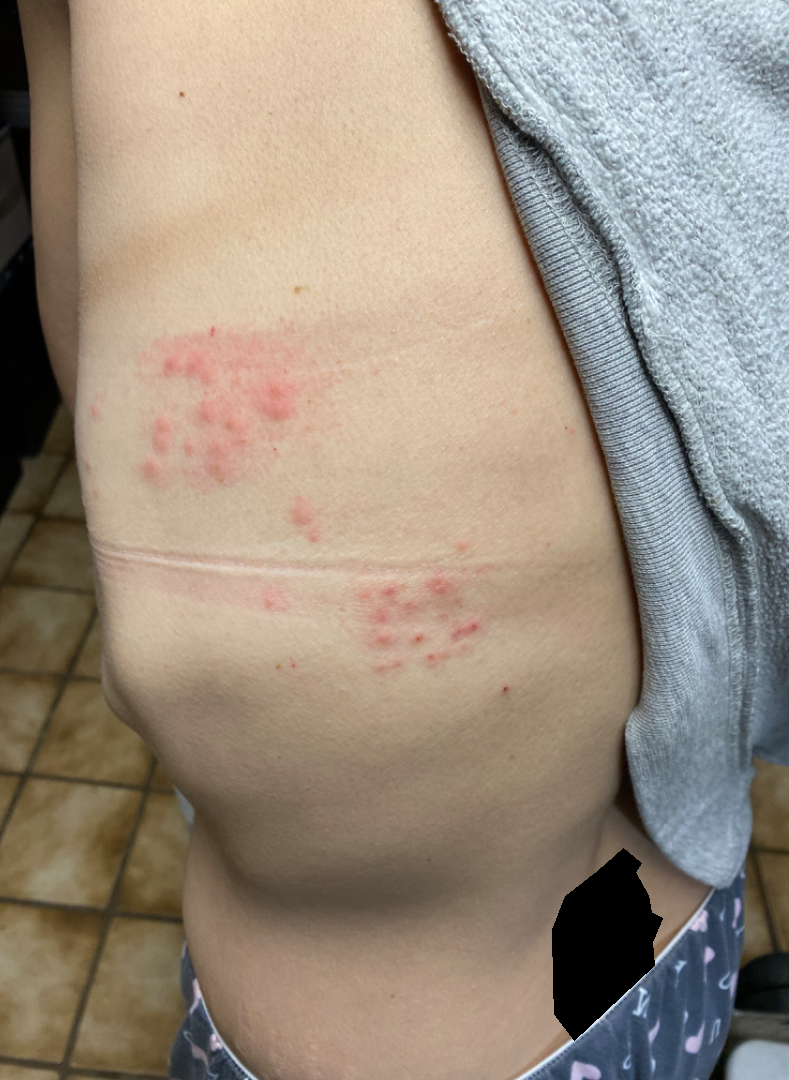Q: How was the photo taken?
A: close-up
Q: Reported symptoms?
A: itching
Q: Any systemic symptoms?
A: none reported
Q: How does the lesion feel?
A: raised or bumpy
Q: How long has this been present?
A: less than one week
Q: Anatomic location?
A: back of the torso
Q: Age and sex?
A: female, age 50–59
Q: What is the differential diagnosis?
A: Herpes Zoster (primary); Allergic Contact Dermatitis (possible); Herpes Simplex (possible)